The lesion involves the back of the torso. This is a close-up image. Skin tone: Fitzpatrick skin type II; human graders estimated MST 2 or 3. Male subject, age 18–29. The patient reports the lesion is flat. No constitutional symptoms were reported. Reported duration is one to four weeks. Symptoms reported: itching: 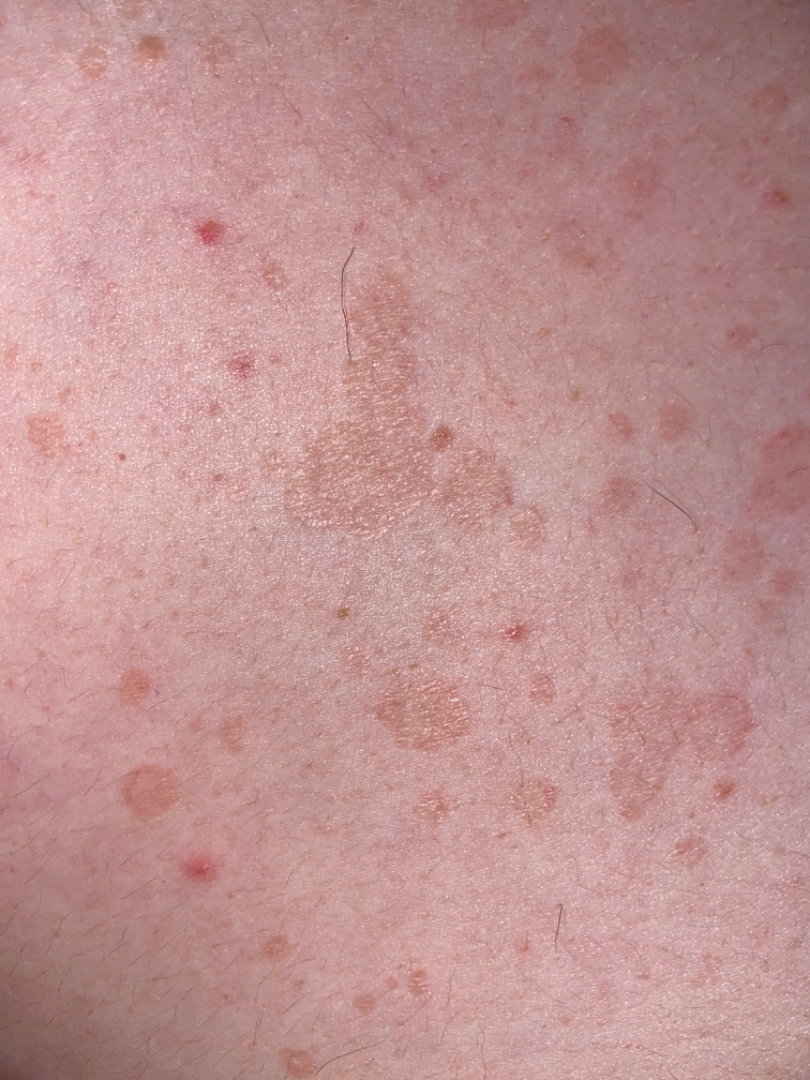assessment=the leading consideration is Tinea Versicolor; less likely is Pityriasis rosea; lower on the differential is Seborrheic Dermatitis; less probable is Tinea; a more distant consideration is Eczema.